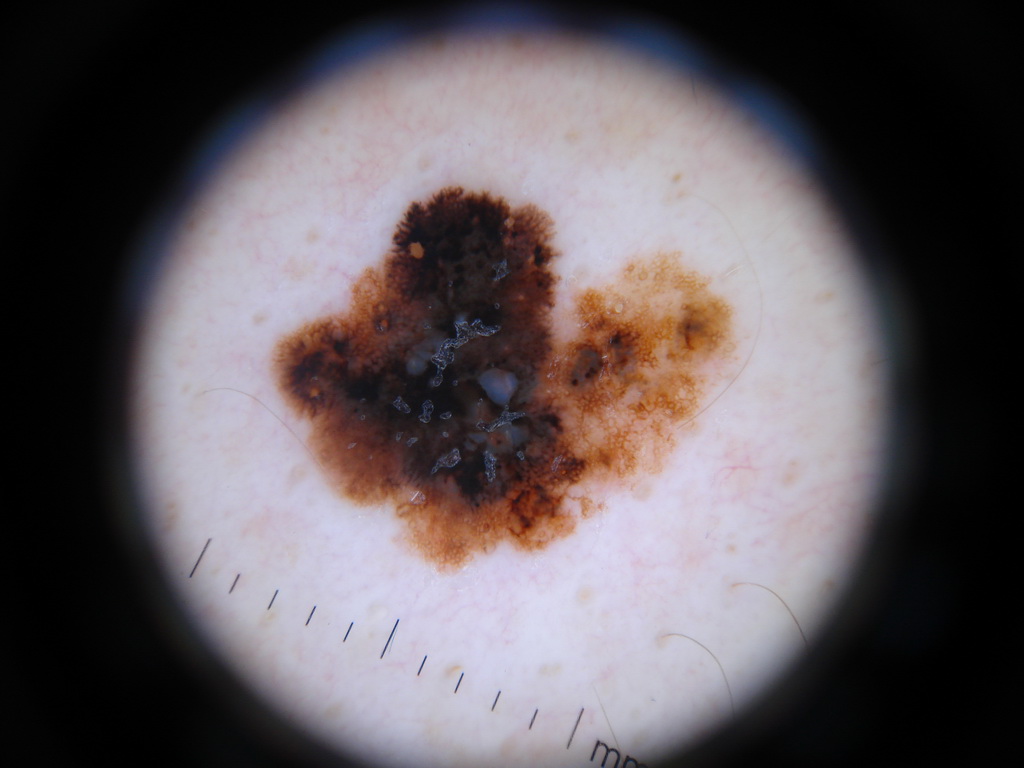Findings:
- modality · dermoscopic image
- subject · male, roughly 50 years of age
- bounding box · [268, 179, 735, 568]
- size · ~14% of the field
- dermoscopic features · pigment network, streaks, and globules
- assessment · a melanoma, a malignancy